An image taken at an angle · the patient is 18–29, female · located on the leg: 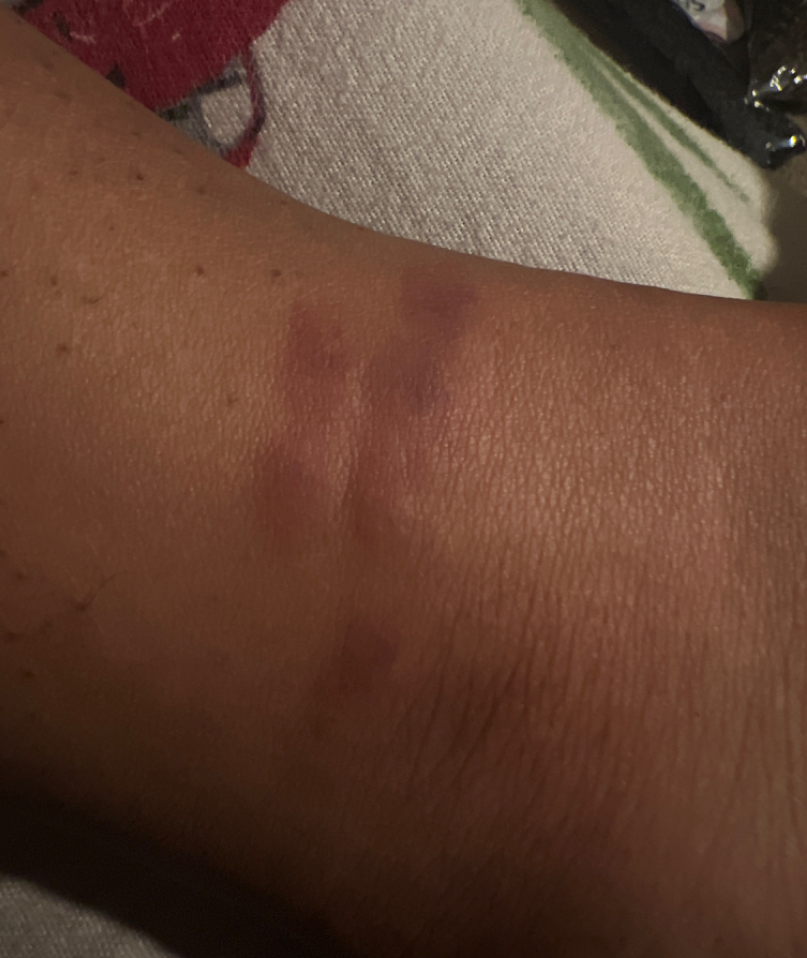Q: Texture?
A: raised or bumpy and flat
Q: What is the patient's skin tone?
A: Fitzpatrick skin type V; lay graders estimated Monk Skin Tone 8 (US pool) or 4 (India pool)
Q: When did this start?
A: one to four weeks
Q: What symptoms does the patient report?
A: itching
Q: Any systemic symptoms?
A: none reported
Q: Patient's own categorization?
A: a rash
Q: What is the dermatologist's impression?
A: Allergic Contact Dermatitis (50%); Insect Bite (33%); Eczema (17%)